This is a dermoscopic photograph of a skin lesion:
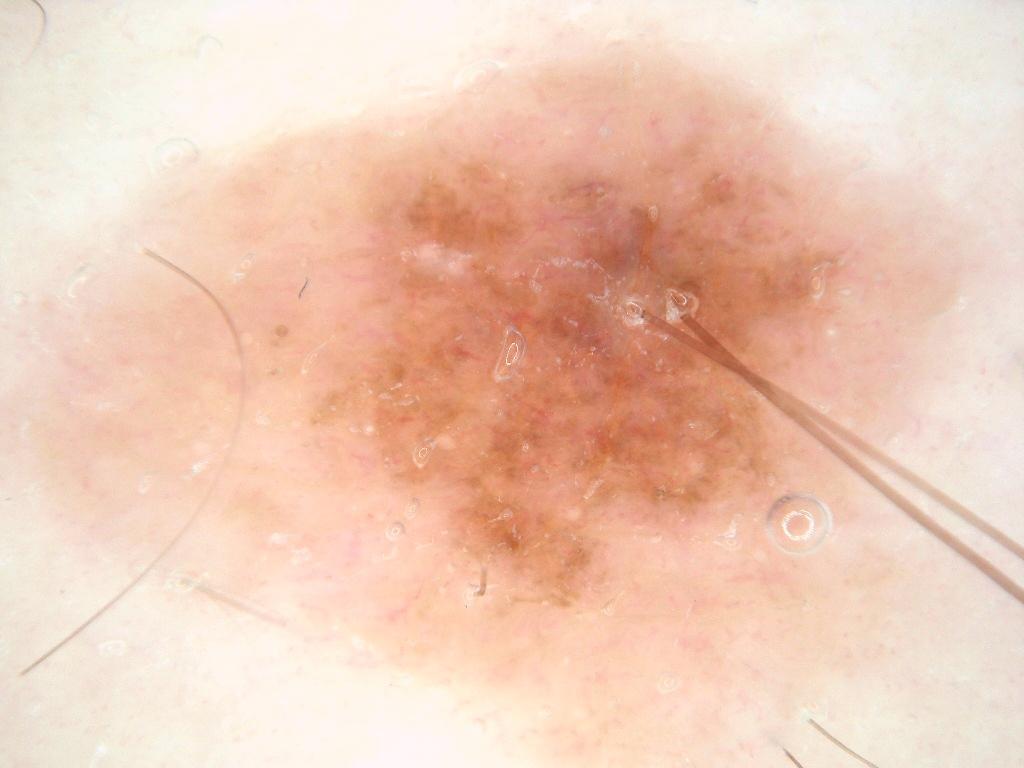<record>
<lesion_location>
  <bbox_xyxy>7, 37, 935, 762</bbox_xyxy>
</lesion_location>
<diagnosis>
  <name>melanocytic nevus</name>
  <malignancy>benign</malignancy>
  <lineage>melanocytic</lineage>
  <provenance>clinical</provenance>
</diagnosis>
</record>